Located on the back of the hand. Female contributor, age 60–69. The photograph was taken at a distance.
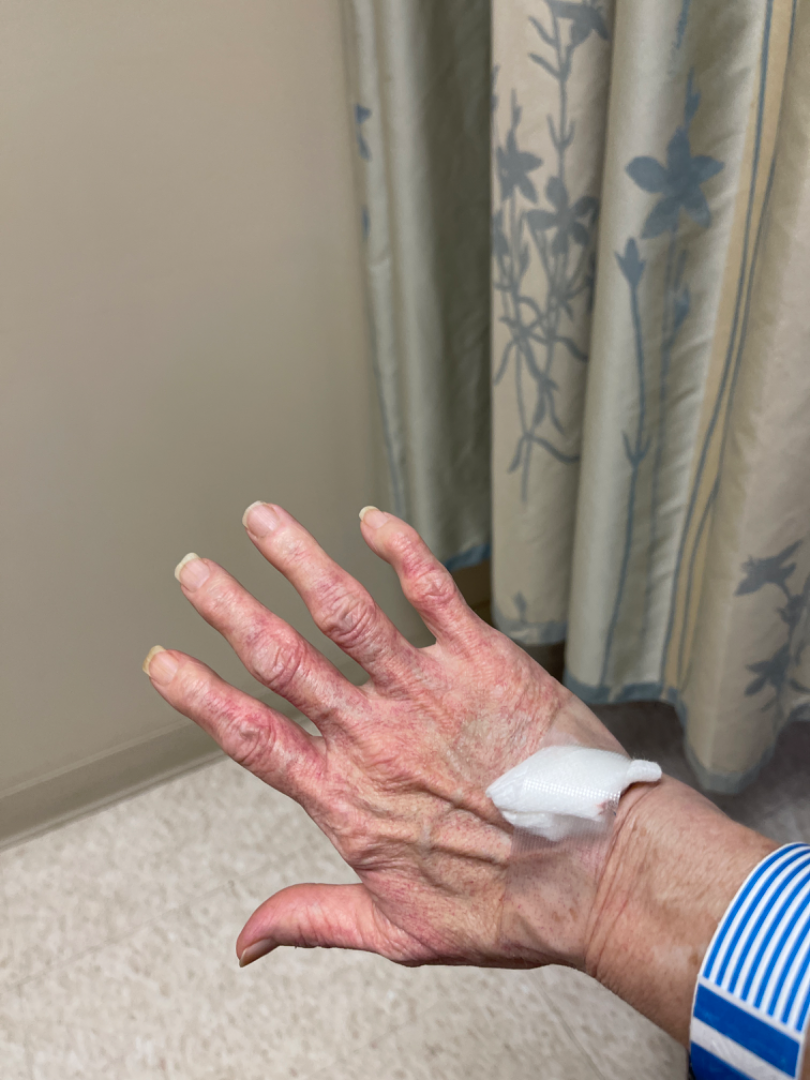The image was not sufficient for the reviewer to characterize the skin condition.
The condition has been present for about one day.
No relevant systemic symptoms.
The patient indicates the lesion is raised or bumpy.